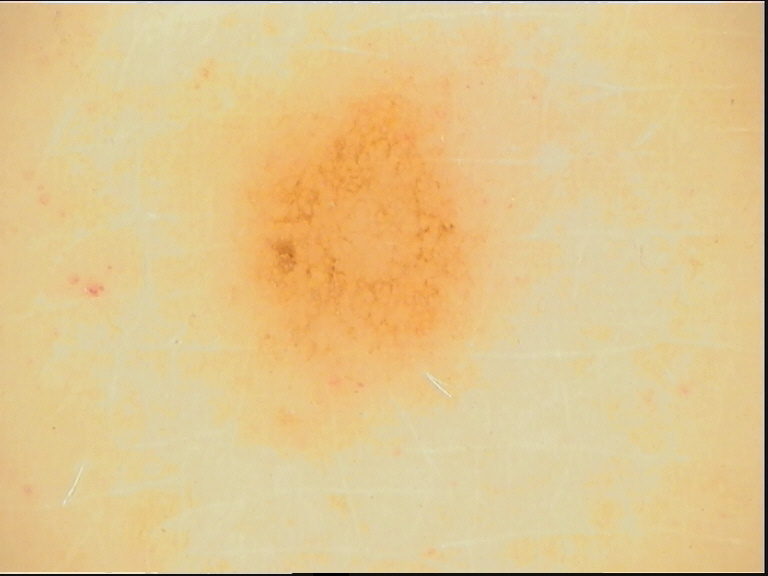Impression:
The diagnosis was a benign lesion — a dysplastic junctional nevus.